A skin lesion imaged with a dermatoscope.
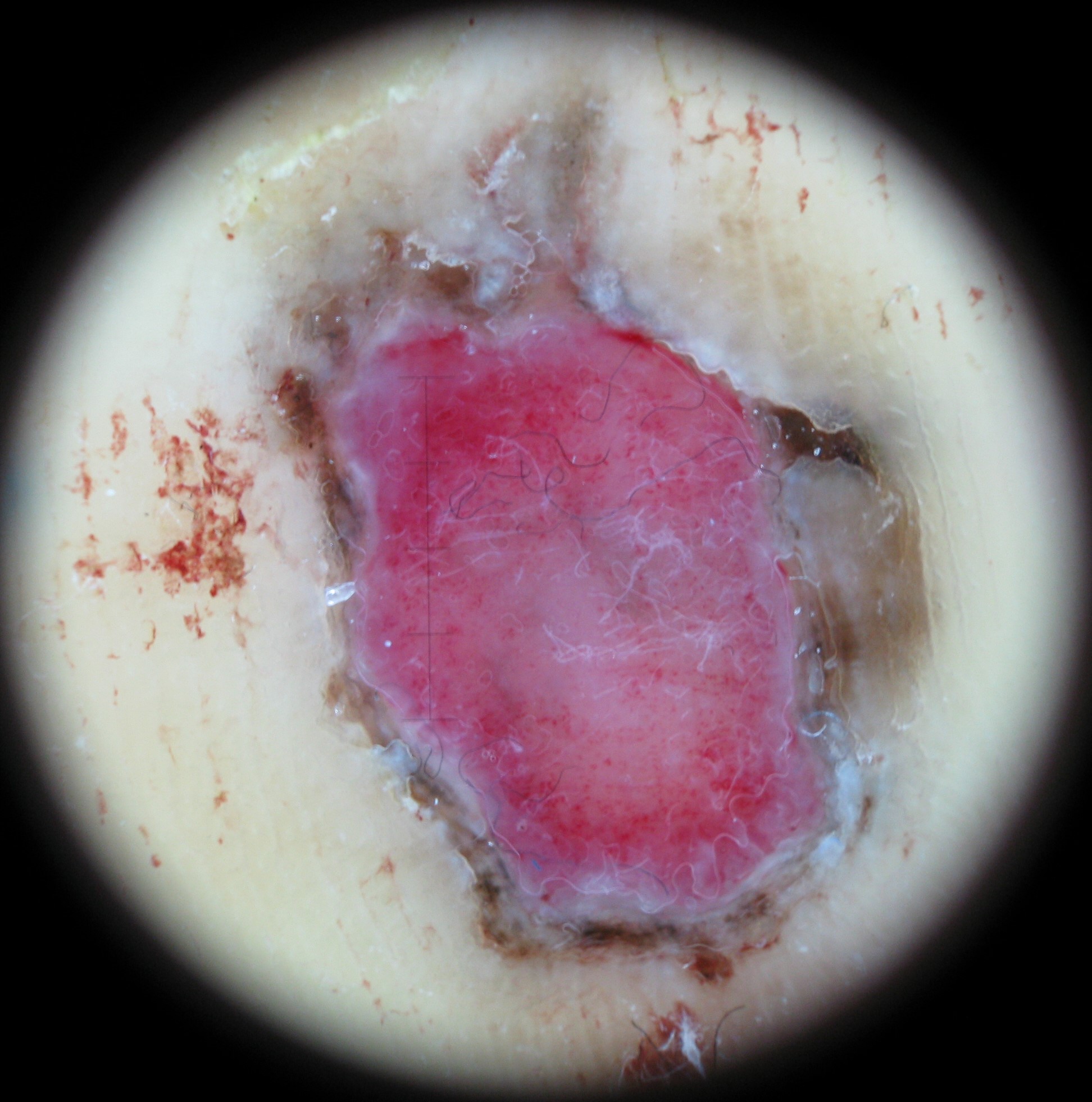Q: What is the diagnosis?
A: acral nodular melanoma (biopsy-proven)